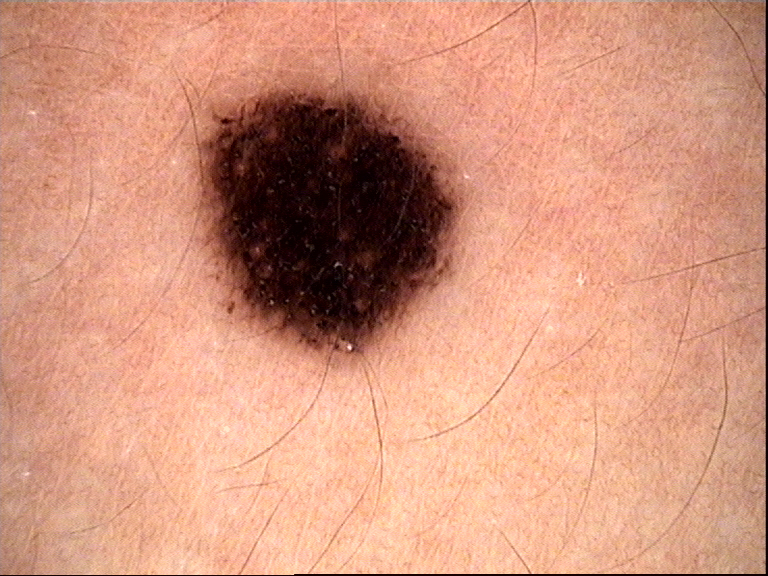A dermoscopic image of a skin lesion. Consistent with a benign lesion — a dysplastic compound nevus.